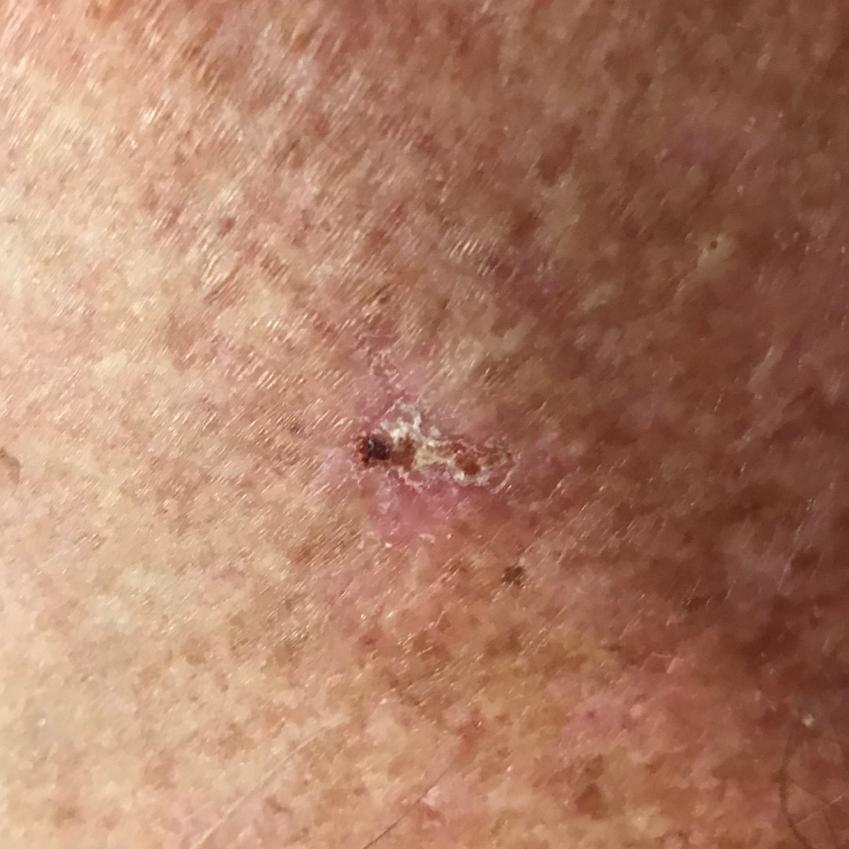A patient 51 years of age. A clinical close-up photograph of a skin lesion. The lesion is on the neck. The patient describes that the lesion itches and is elevated, but does not hurt. The clinical impression was an actinic keratosis.